The photograph was taken at an angle.
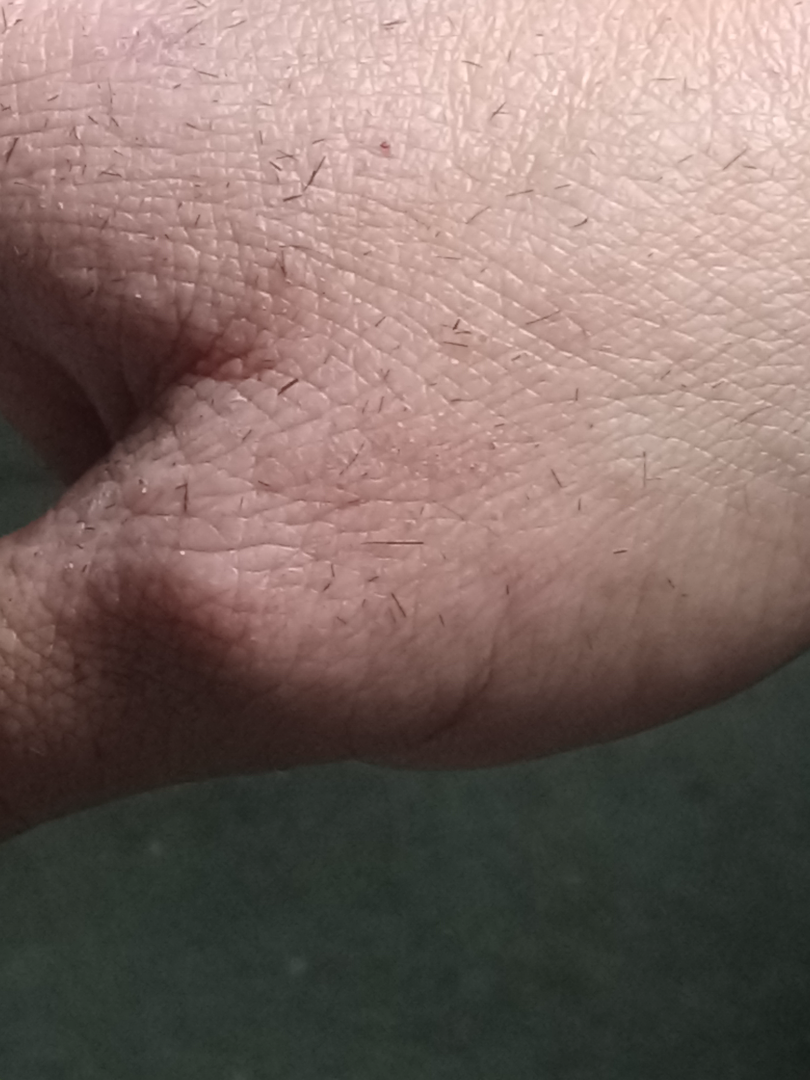assessment: not assessable.